This is a dermoscopic photograph of a skin lesion:
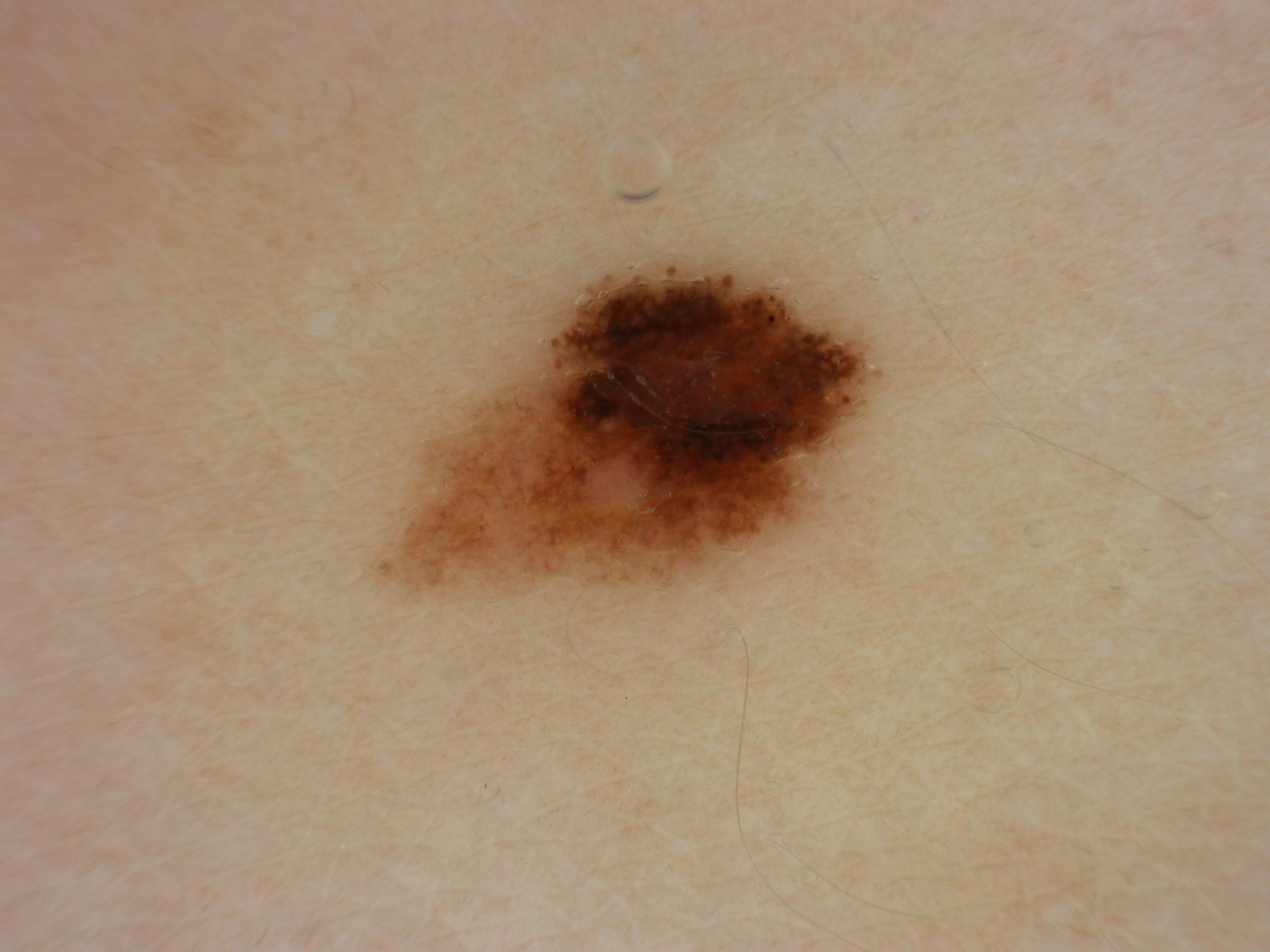<case>
<lesion_location>
  <bbox_xyxy>358, 262, 887, 615</bbox_xyxy>
</lesion_location>
<dermoscopic_features>
  <present>pigment network, globules</present>
  <absent>streaks, milia-like cysts, negative network</absent>
</dermoscopic_features>
<diagnosis>
  <name>melanoma</name>
  <malignancy>malignant</malignancy>
  <lineage>melanocytic</lineage>
  <provenance>histopathology</provenance>
</diagnosis>
</case>